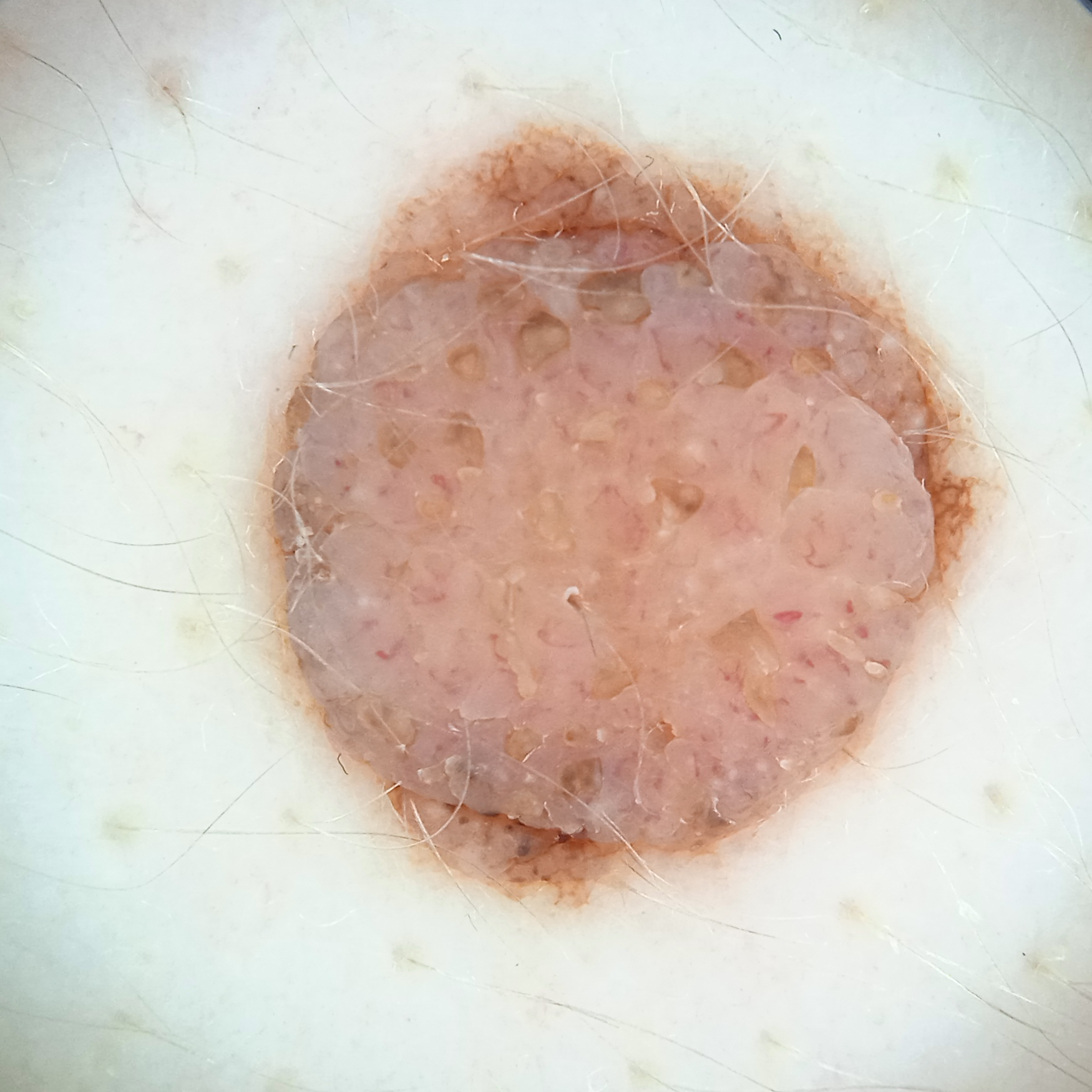Q: What was the diagnosis?
A: melanocytic nevus (dermatologist consensus)